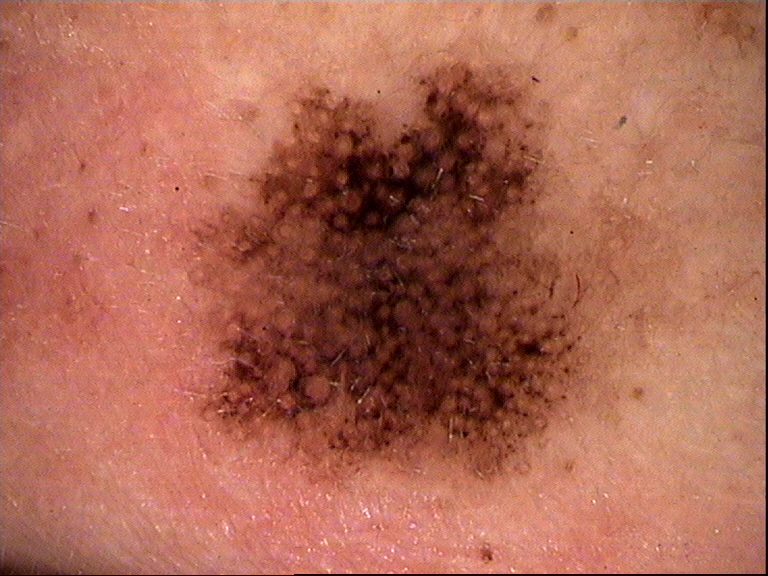A dermoscopic image of a skin lesion. The architecture is that of a keratinocytic lesion. Labeled as a seborrheic keratosis.